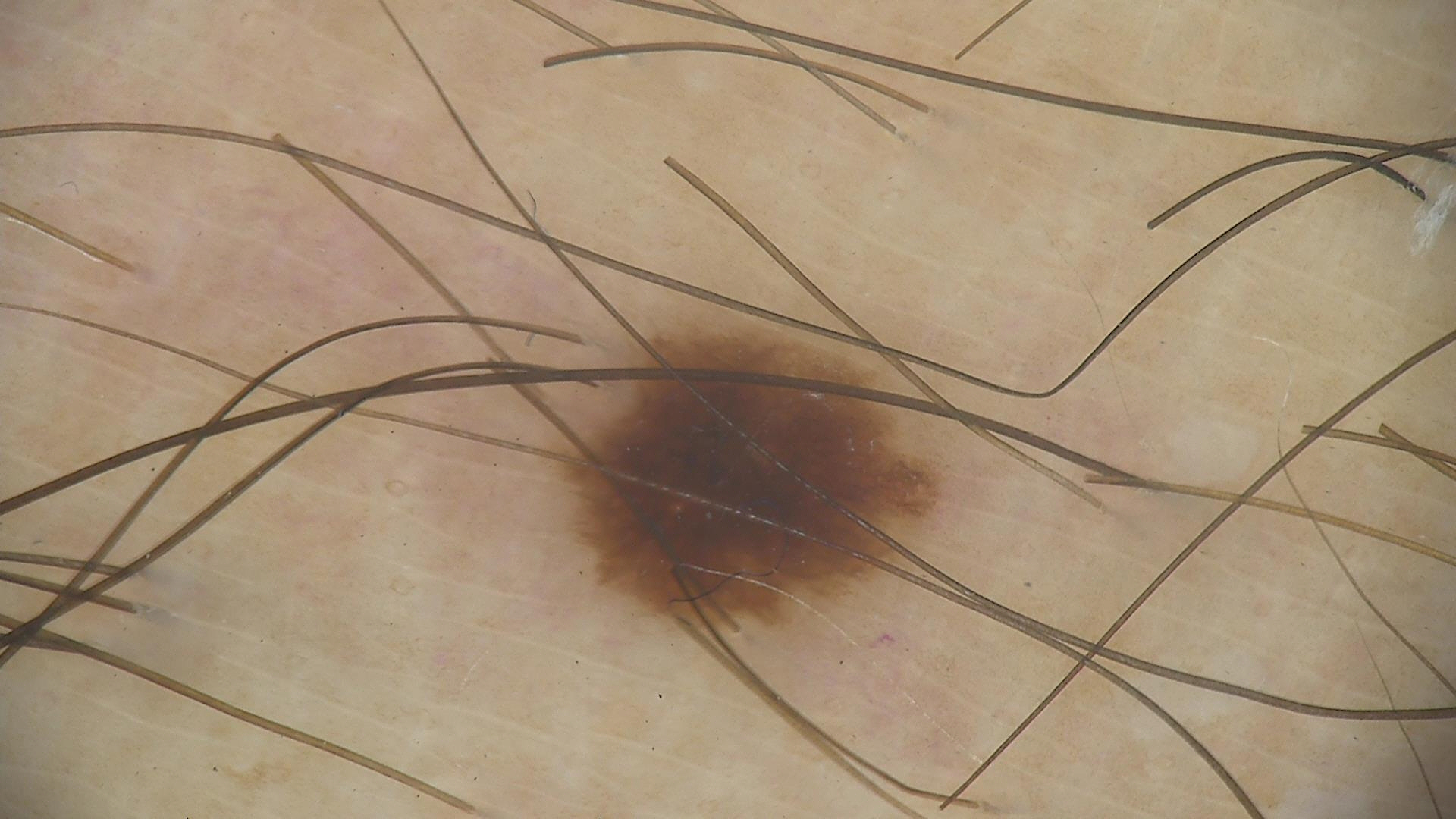Summary: A dermoscopic close-up of a skin lesion. Conclusion: The diagnostic label was a dysplastic junctional nevus.